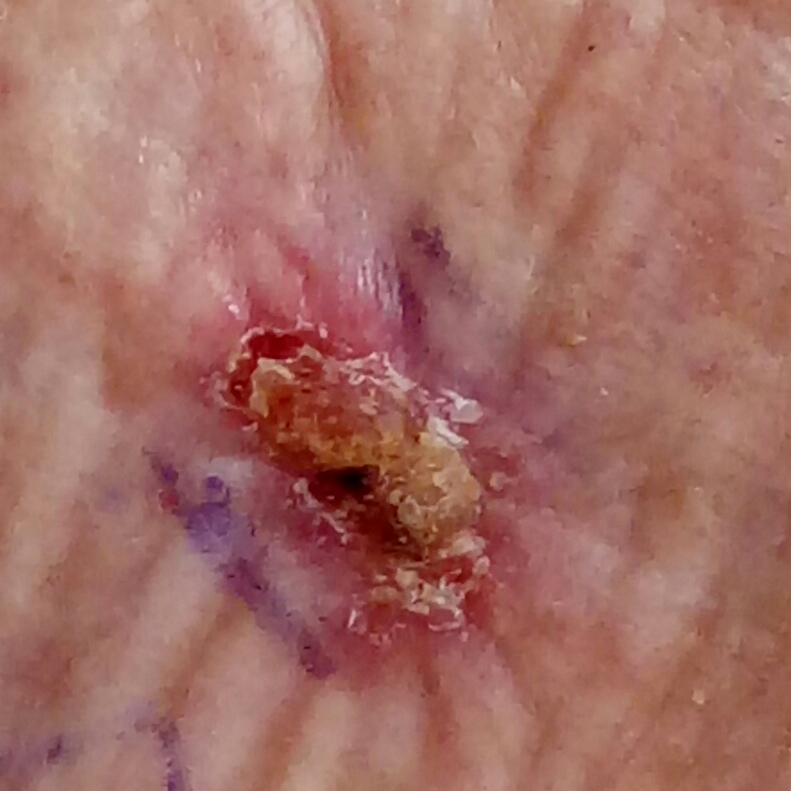Conclusion: Histopathology confirmed a basal cell carcinoma.